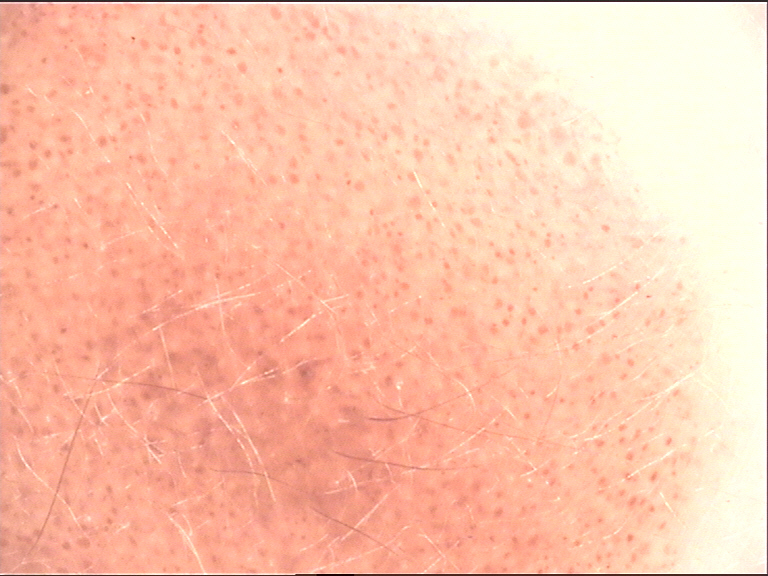Findings: A dermoscopic close-up of a skin lesion. Impression: Diagnosed as a congenital junctional nevus.